A male patient approximately 80 years of age, a dermoscopic view of a skin lesion.
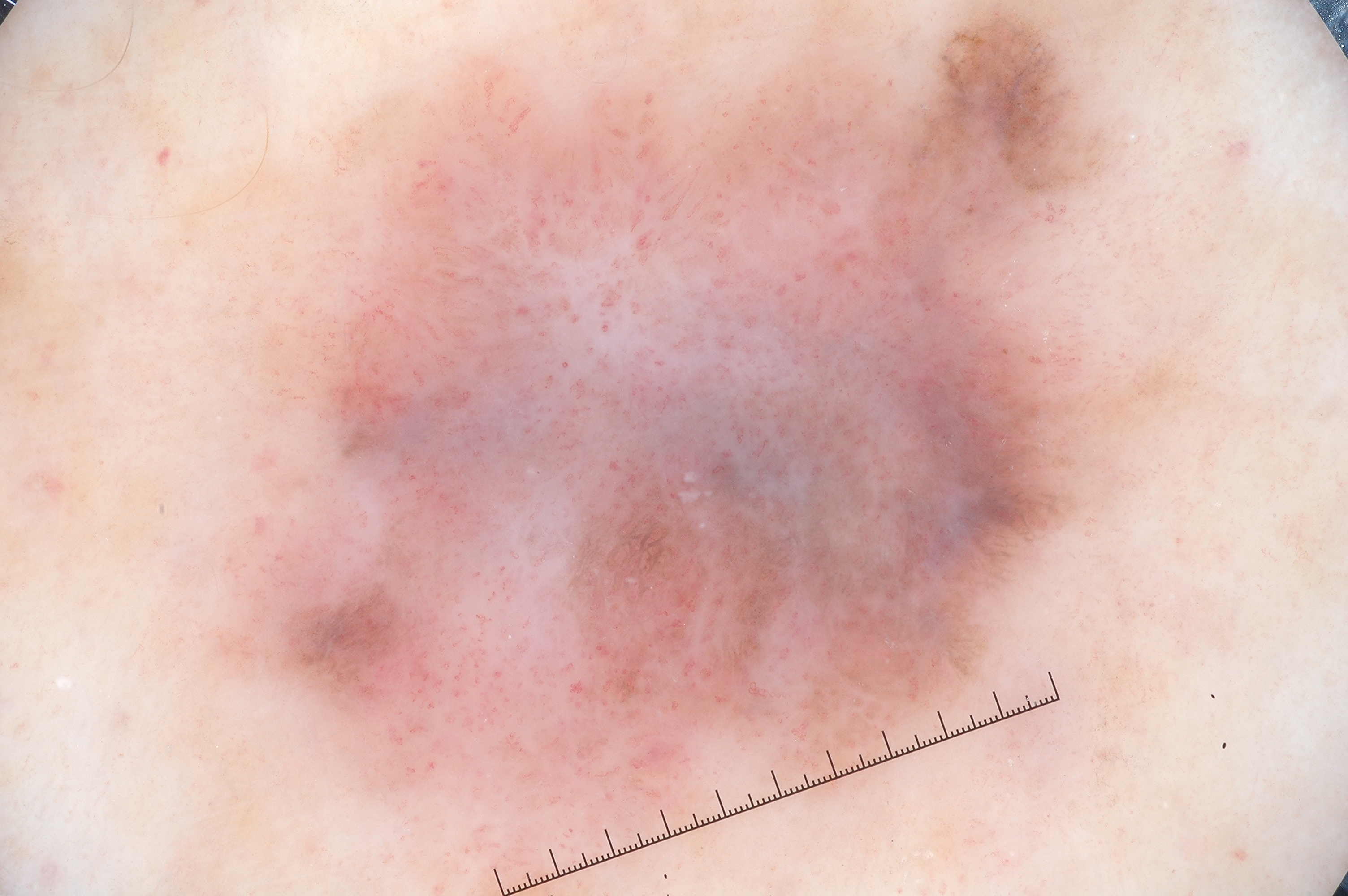Case summary:
The lesion occupies roughly 54% of the field. With coordinates (x1, y1, x2, y2), the lesion occupies the region 190/0/1190/895. Dermoscopy demonstrates negative network and pigment network; no streaks or milia-like cysts. The lesion extends to the edge of the dermoscopic field.
Diagnosis:
Histopathologically confirmed as a melanoma, a malignant lesion.